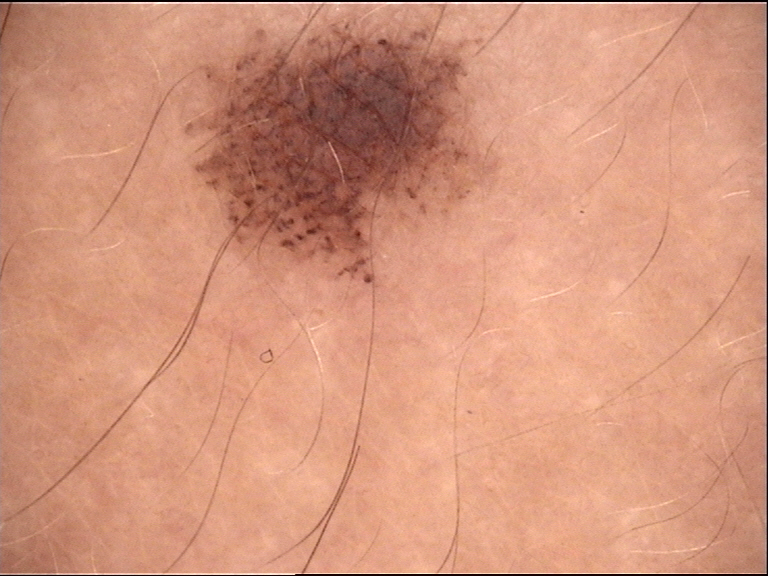Q: What kind of image is this?
A: dermoscopy
Q: What is this lesion?
A: dysplastic junctional nevus (expert consensus)